The patient says their skin reddens with sun exposure. The patient describes having a moderate number of moles. Dermoscopy of a skin lesion. By self-report, no sunbed use and no family history of skin cancer. Collected as part of a research study, without a referral diagnosis. A female subject 59 years old: 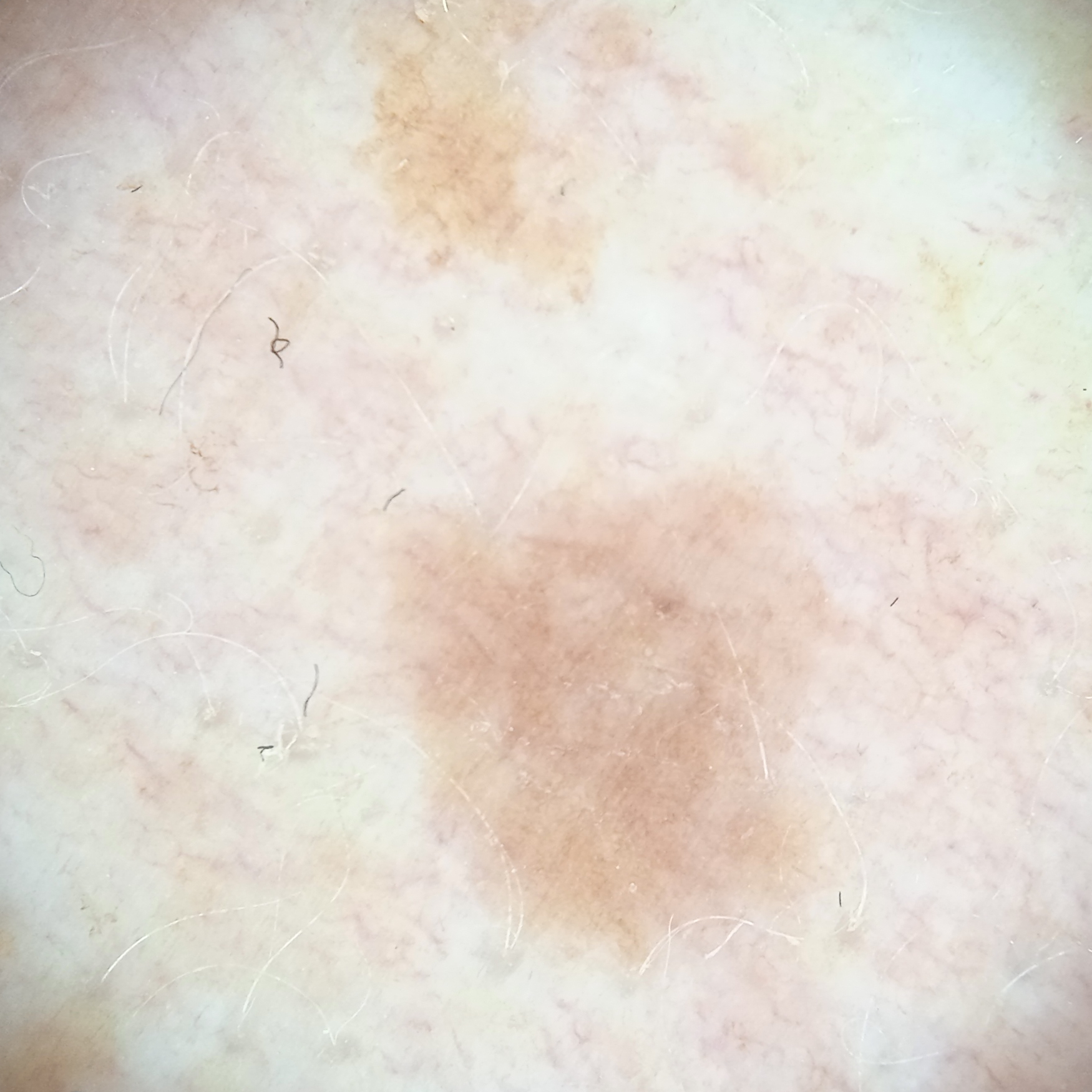Findings:
* site — an arm
* size — 6.5 mm
* diagnostic label — melanocytic nevus (dermatologist consensus)